A dermoscopic photograph of a skin lesion.
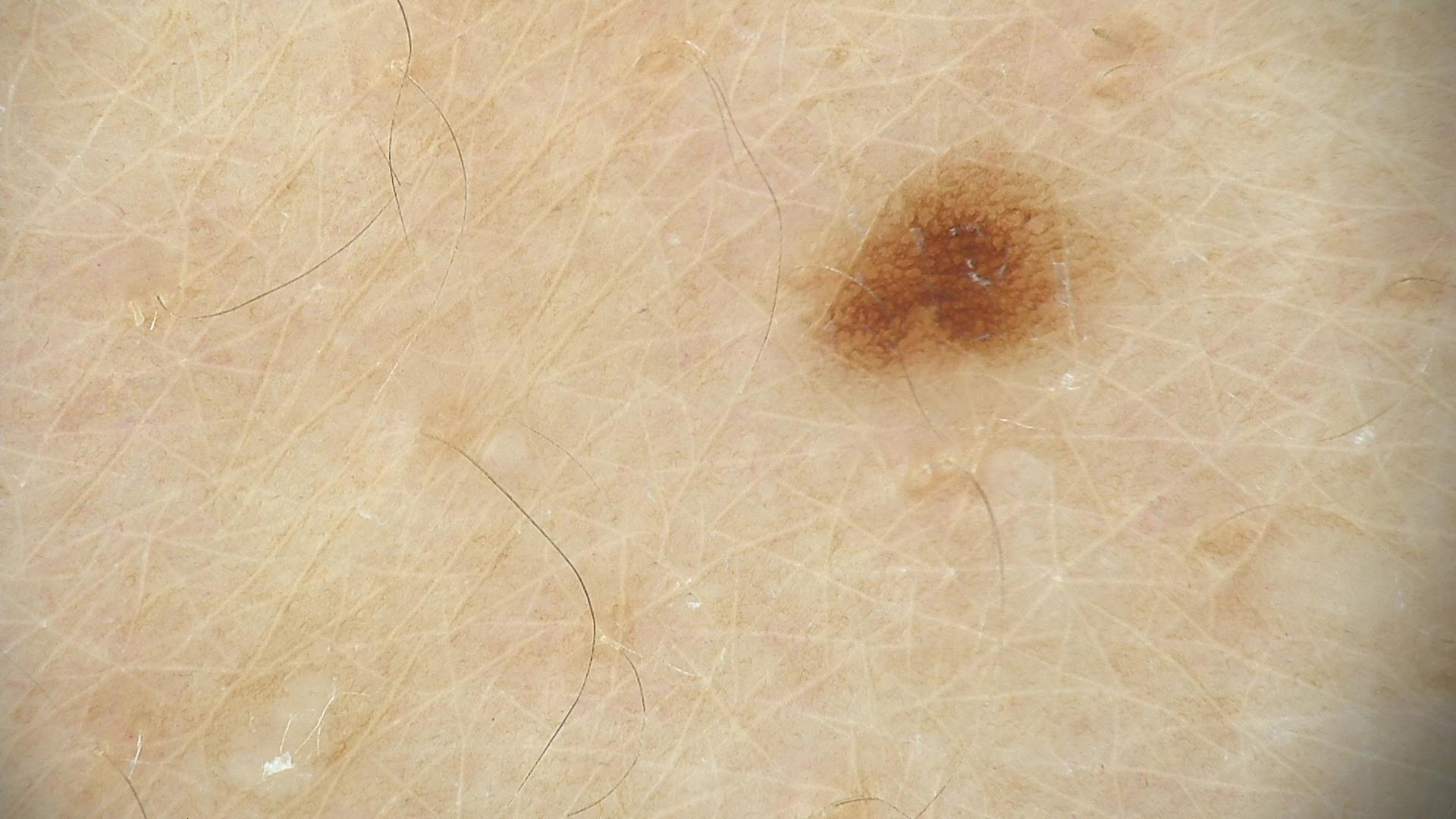The architecture is that of a banal lesion. Diagnosed as a junctional nevus.